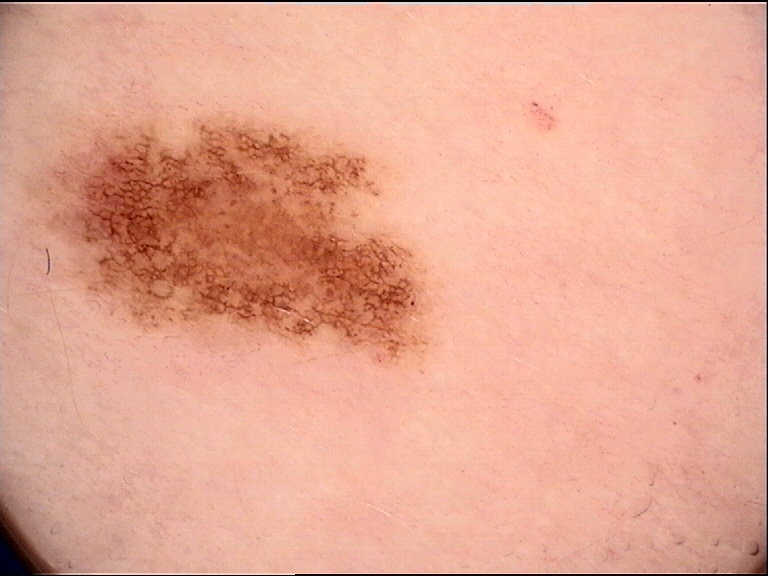Conclusion:
Labeled as a dysplastic junctional nevus.